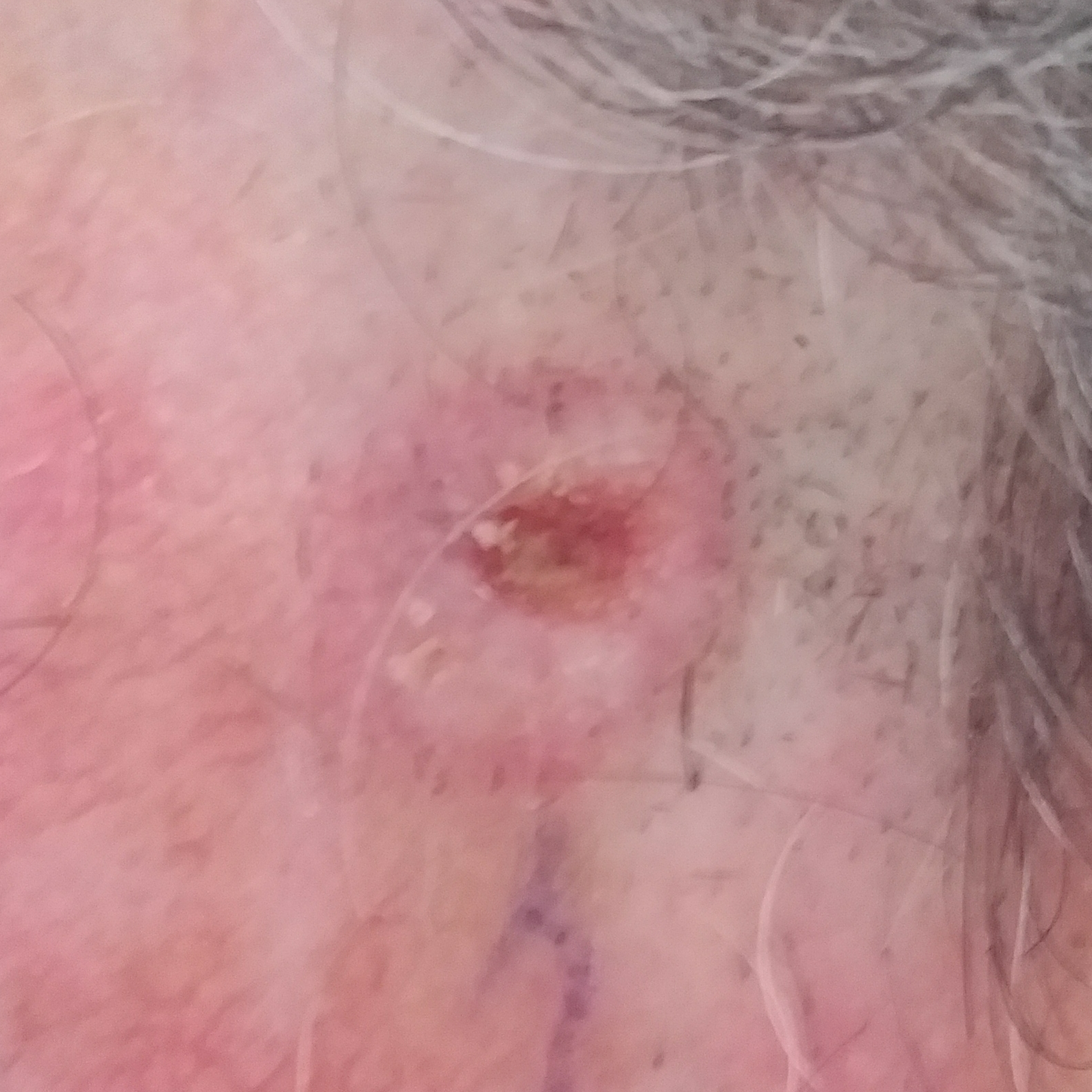A male subject in their late 40s.
A clinical close-up photograph of a skin lesion.
FST II.
The lesion was found on the face.
The lesion is roughly 10 by 10 mm.
By the patient's account, the lesion is elevated, has grown, itches, and has bled, but has not changed.
Confirmed on histopathology as a basal cell carcinoma.